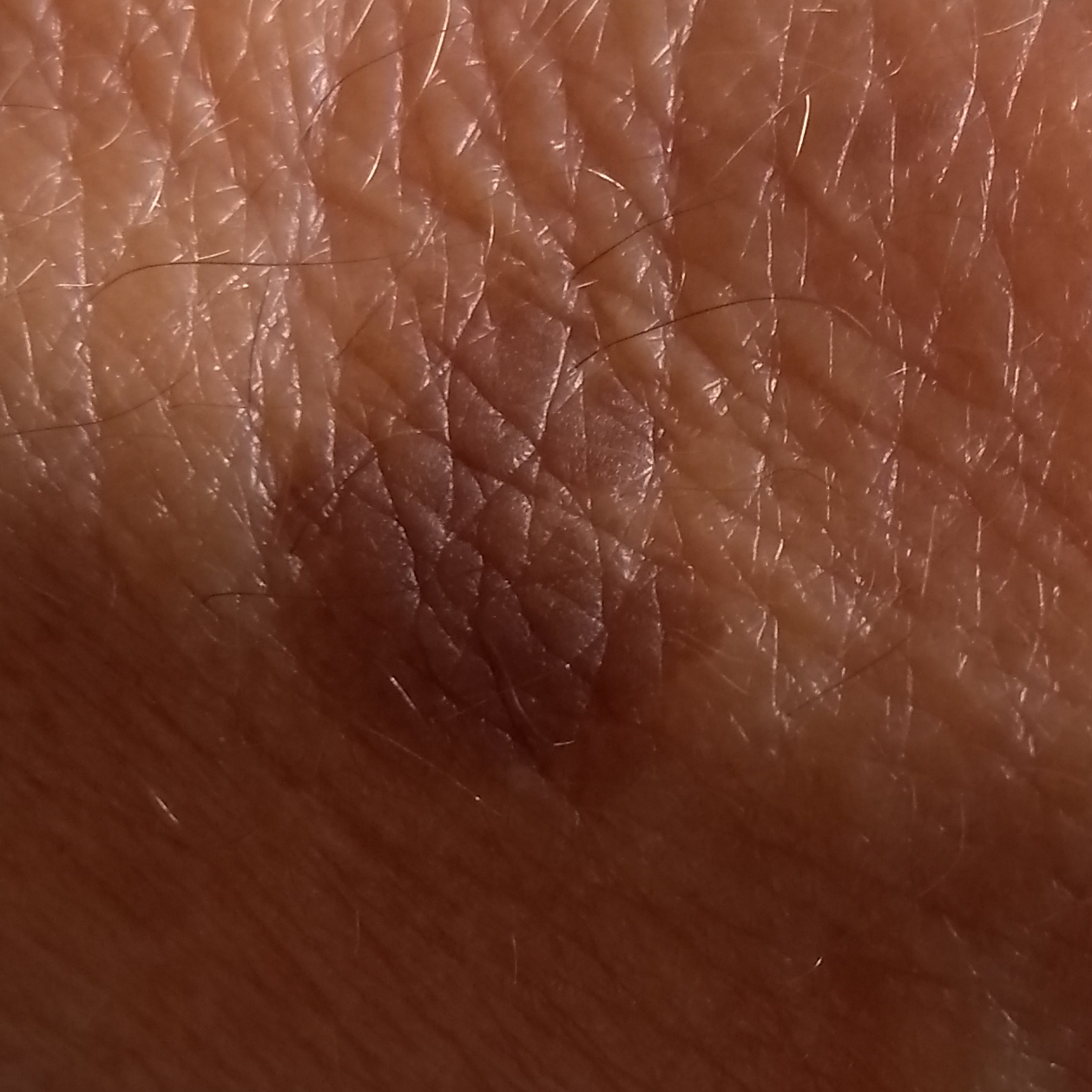* subject · aged 65
* patient-reported symptoms · itching / no change in appearance, no elevation
* assessment · seborrheic keratosis (clinical consensus)